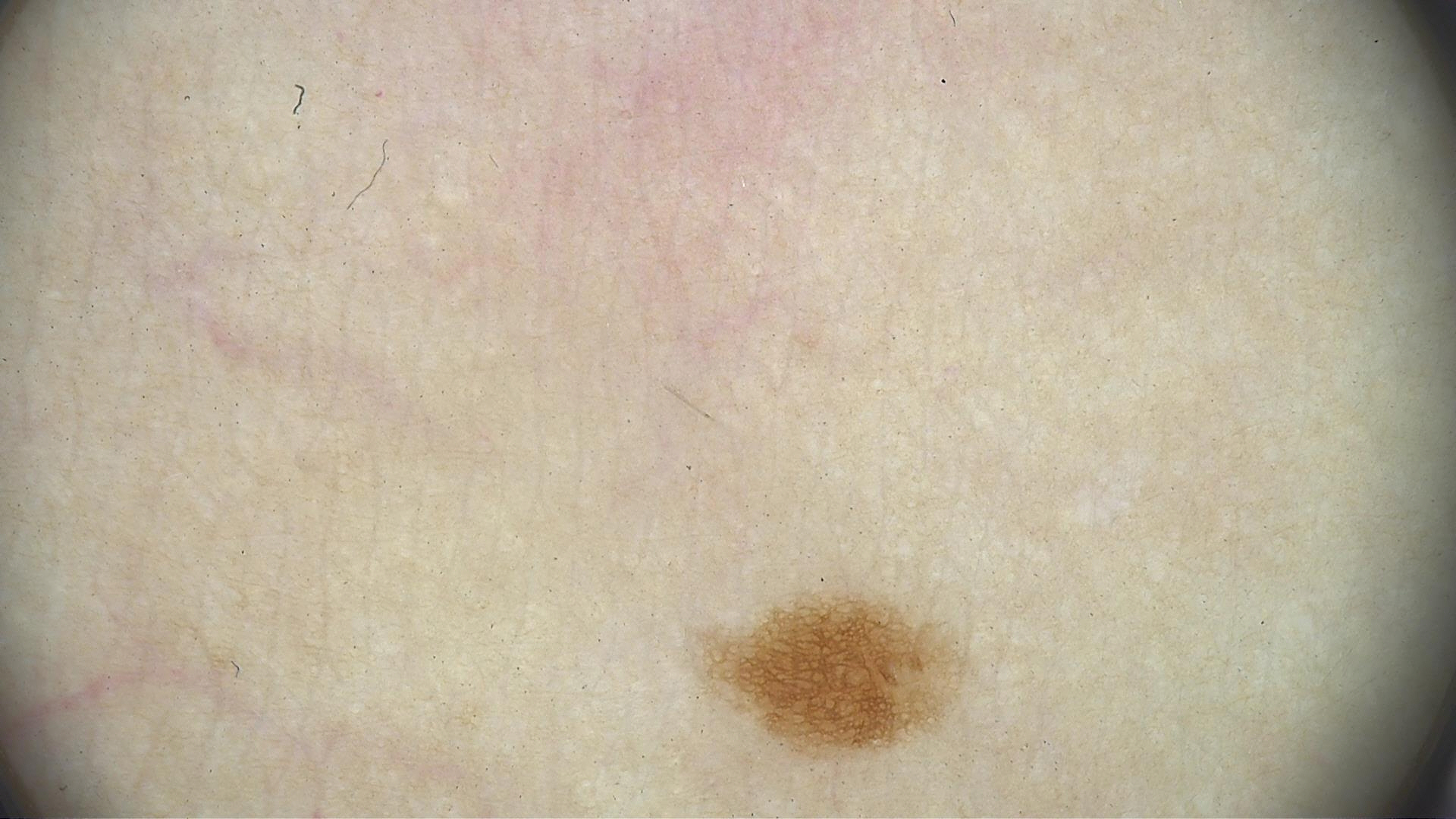image=dermatoscopy | assessment=junctional nevus (expert consensus).